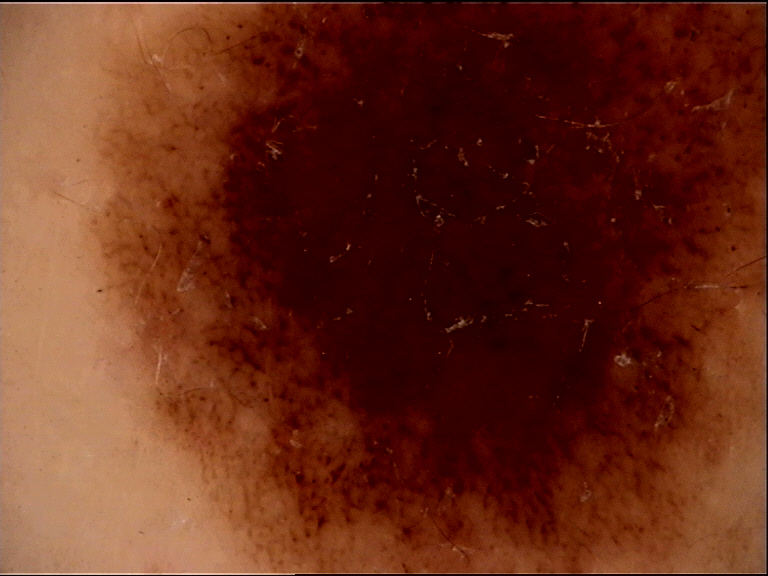Case:
* assessment · dysplastic compound nevus (expert consensus)